Imaged for a research study, with no referral diagnosis recorded · a female subject aged 81 · dermoscopy of a skin lesion — 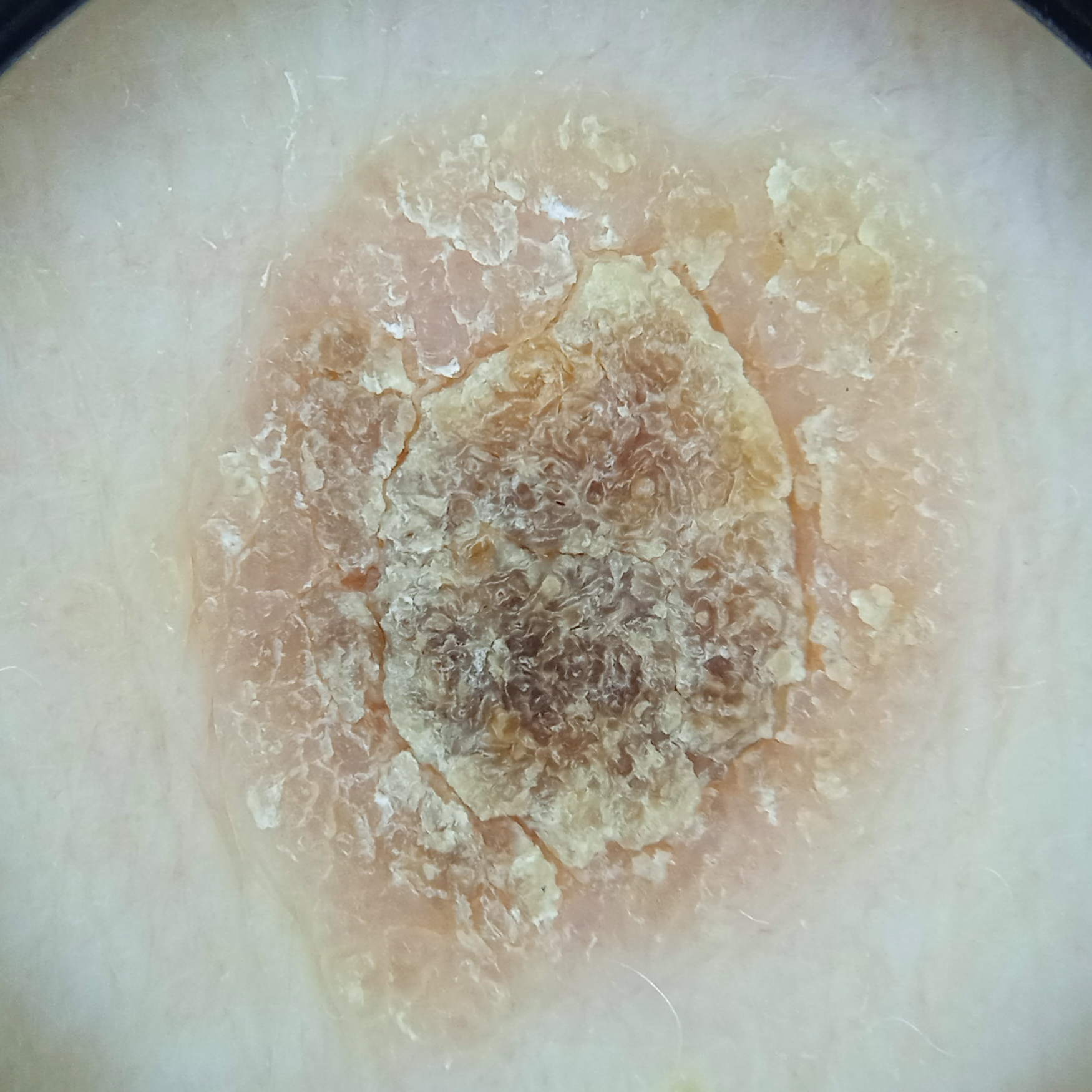Findings:
The lesion is located on the back. The lesion is about 9.8 mm across.
Conclusion:
The diagnostic impression was a seborrheic keratosis.